The photograph was taken at an angle. The lesion is described as raised or bumpy. No constitutional symptoms were reported. Skin tone: Fitzpatrick skin type II. The patient described the issue as a rash. The patient is male. The leg is involved: 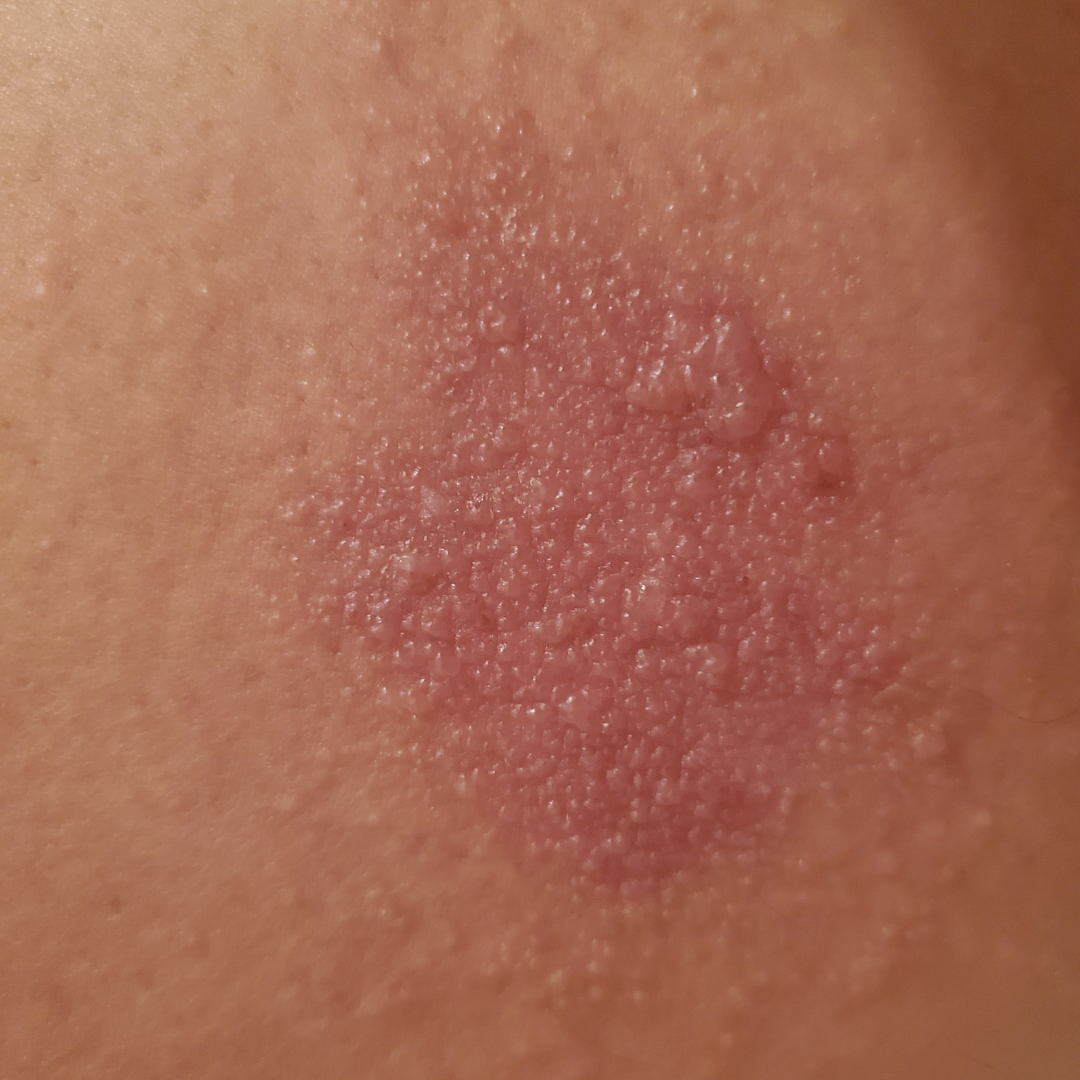Case summary:
• dermatologist impression: most likely Allergic Contact Dermatitis